The lesion involves the arm. The contributor notes the lesion is fluid-filled. The contributor notes the condition has been present for about one day. The contributor notes associated fever, chills and joint pain. Skin tone: self-reported FST I; human graders estimated MST 1 (US pool) or 2 (India pool). The contributor is 18–29, female. Self-categorized by the patient as a rash. The lesion is associated with bothersome appearance, enlargement, pain, burning and itching. A close-up photograph: 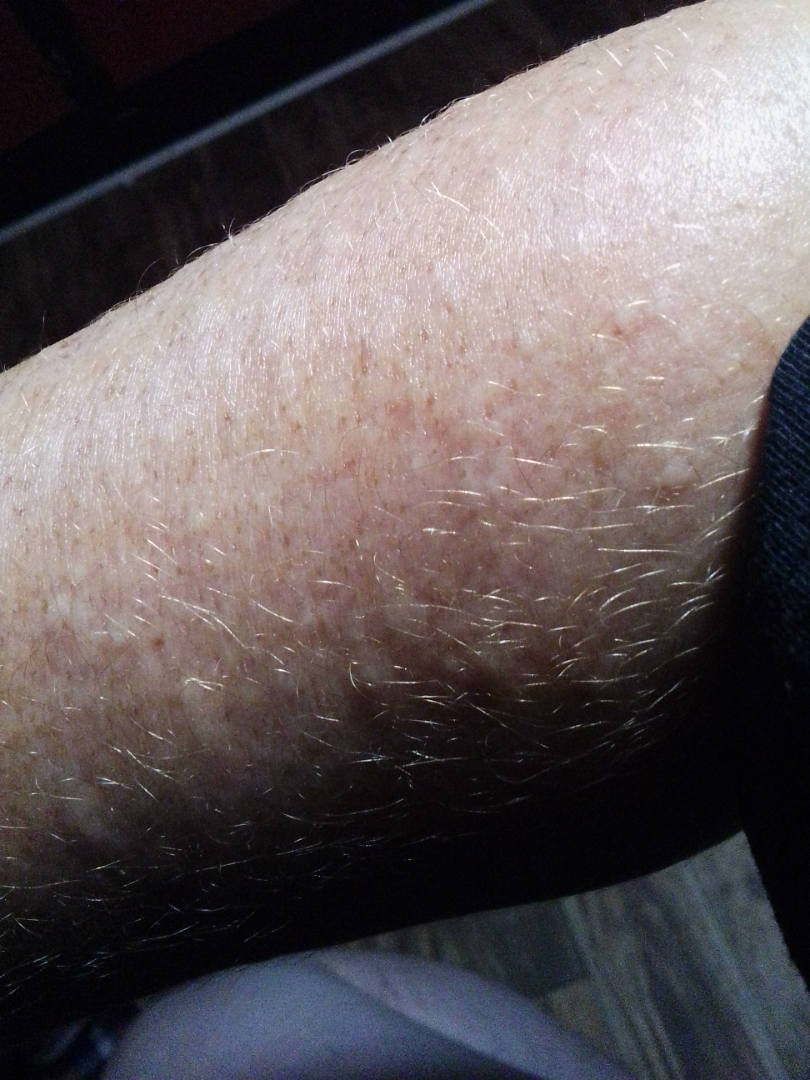The skin findings could not be characterized from the image.